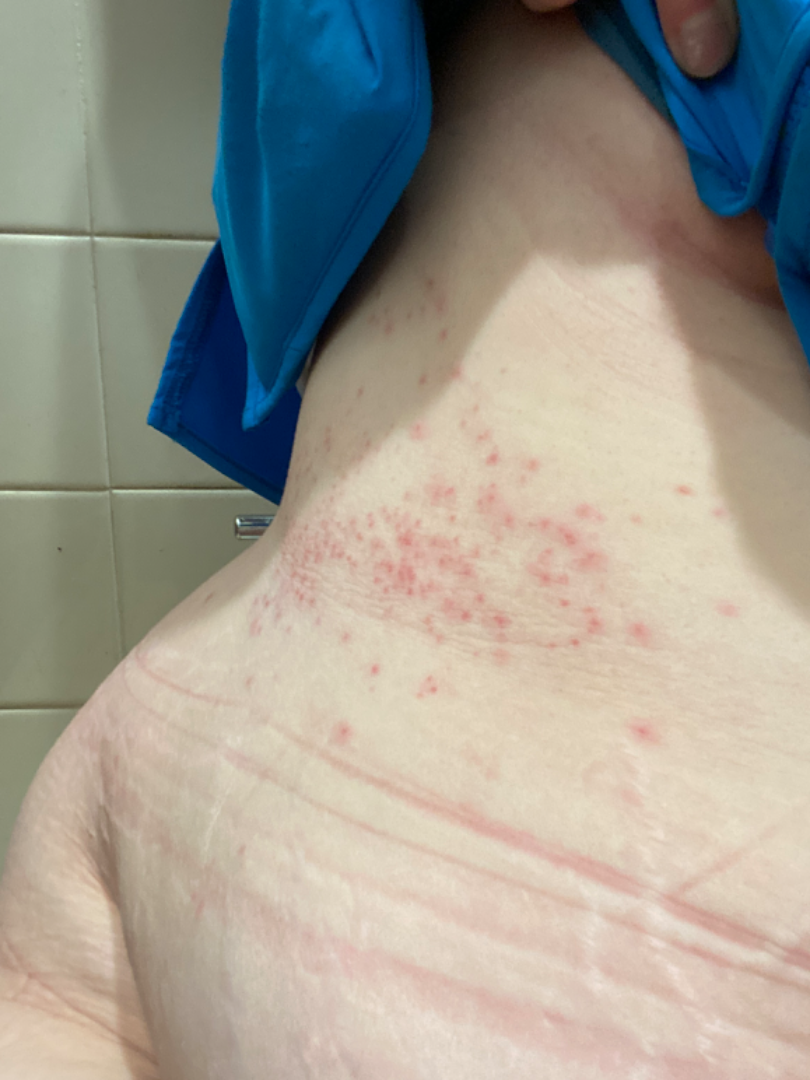The photo was captured at an angle.
Intertrigo (considered); Herpes Zoster (considered); Irritant Contact Dermatitis (remote).